This is a close-up image; skin tone: Fitzpatrick skin type V: 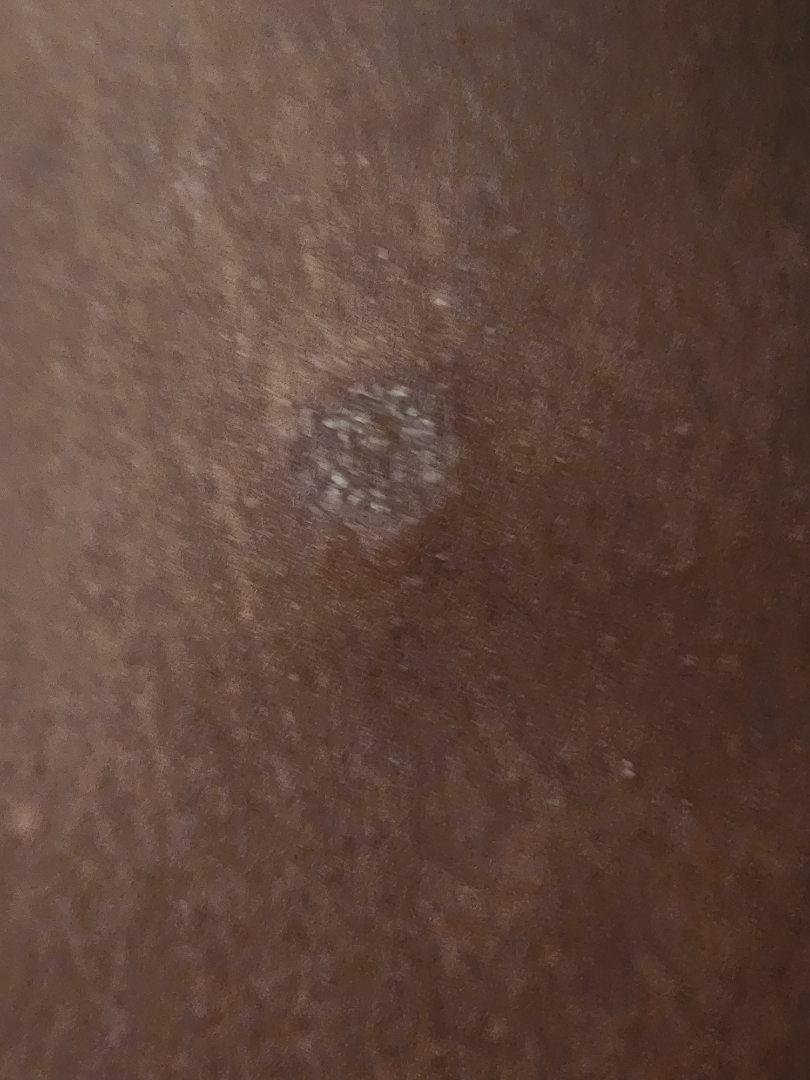On dermatologist assessment of the image: Fungal dermatosis and SCC/SCCIS were considered with similar weight.